A skin lesion imaged with a dermatoscope: 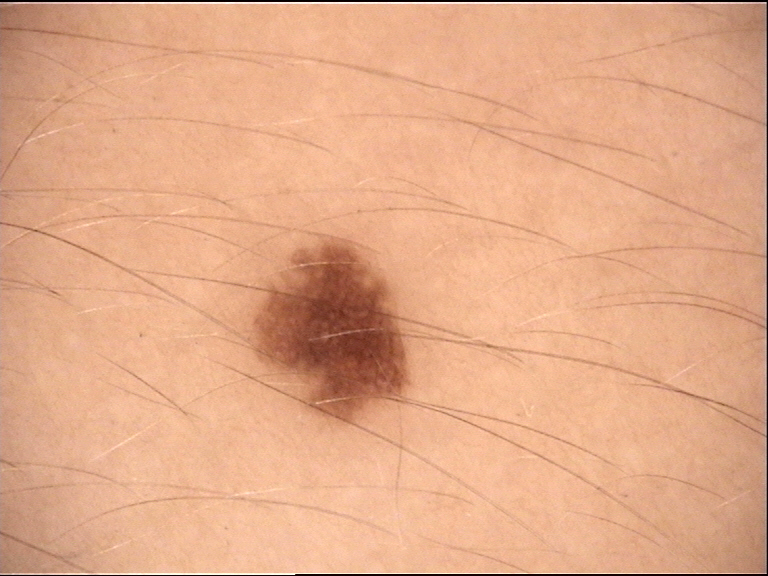{"diagnosis": {"name": "junctional nevus", "code": "jb", "malignancy": "benign", "super_class": "melanocytic", "confirmation": "expert consensus"}}